A dermoscopic image of a skin lesion.
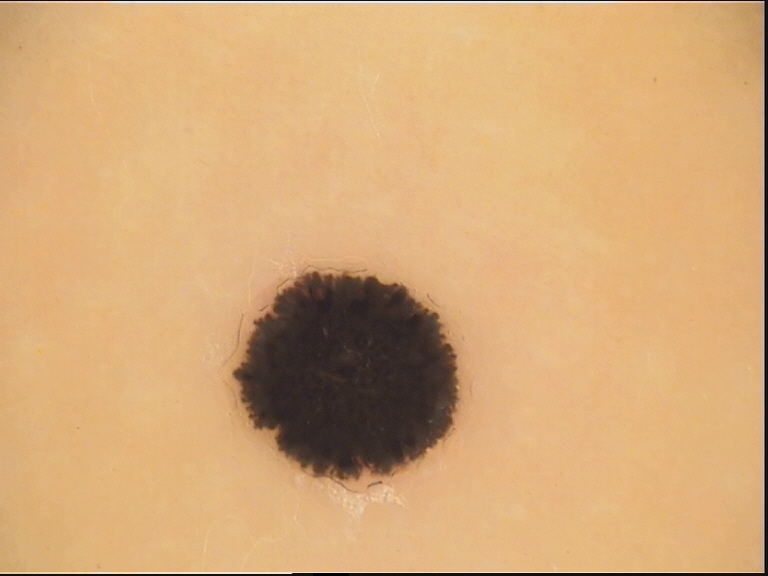The architecture is that of a junctional, dysplastic lesion.
Classified as a Spitz/Reed nevus.